Close-up view. The leg is involved: 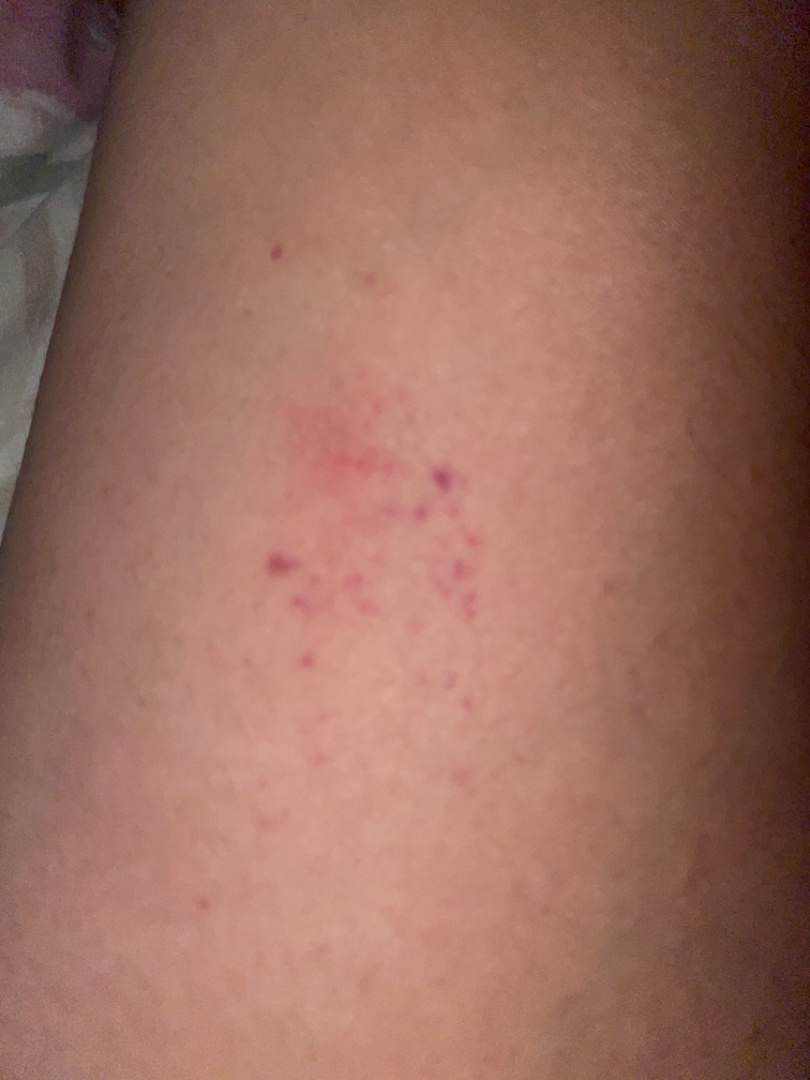Case summary:
- assessment · indeterminate
- surface texture · flat
- patient-reported symptoms · burning and itching
- self-categorized as · a rash
- associated systemic symptoms · none reported